The lesion involves the leg. The subject is a male aged 18–29. The photograph is a close-up of the affected area. The condition has been present for less than one week. The patient reported no systemic symptoms. Self-categorized by the patient as a rash. The lesion is described as raised or bumpy and flat:
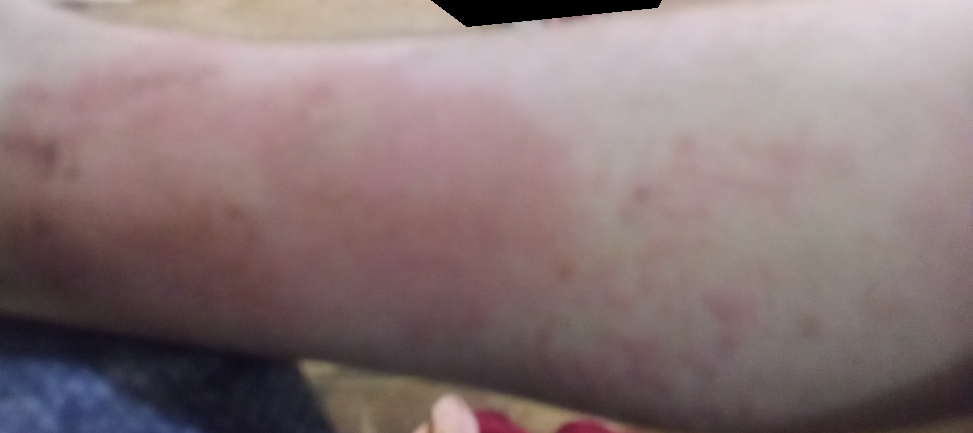The dermatologist could not determine a likely condition from the photograph alone.